A male patient aged 71 · a clinical photo of a skin lesion taken with a smartphone · the patient is Fitzpatrick phototype II · history notes tobacco use, prior malignancy (patient or family), and alcohol use.
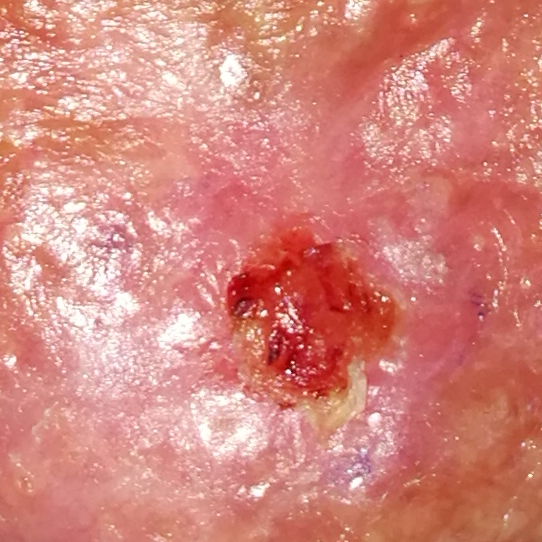The lesion was found on the nose. Measuring about 9 × 9 mm. The biopsy diagnosis was a basal cell carcinoma.